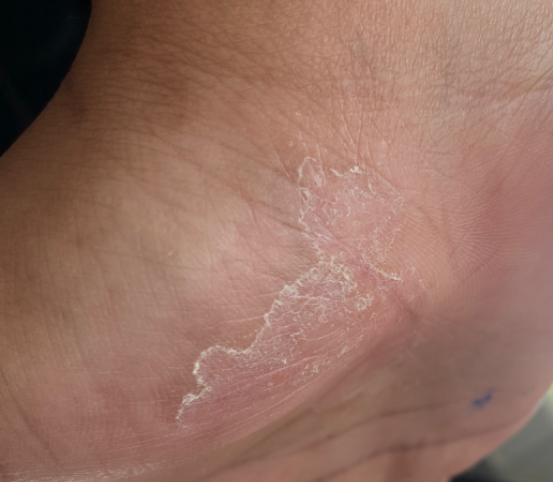Patient information: This image was taken at an angle. Located on the palm and sole of the foot. The lesion is described as rough or flaky. The patient notes itching and burning. The patient described the issue as a rash. Present for three to twelve months. The contributor is 18–29, female. Review: On independent review by the dermatologists: Psoriasis (most likely); Tinea (considered); Irritant Contact Dermatitis (considered); Eczema (lower probability); Allergic Contact Dermatitis (lower probability).